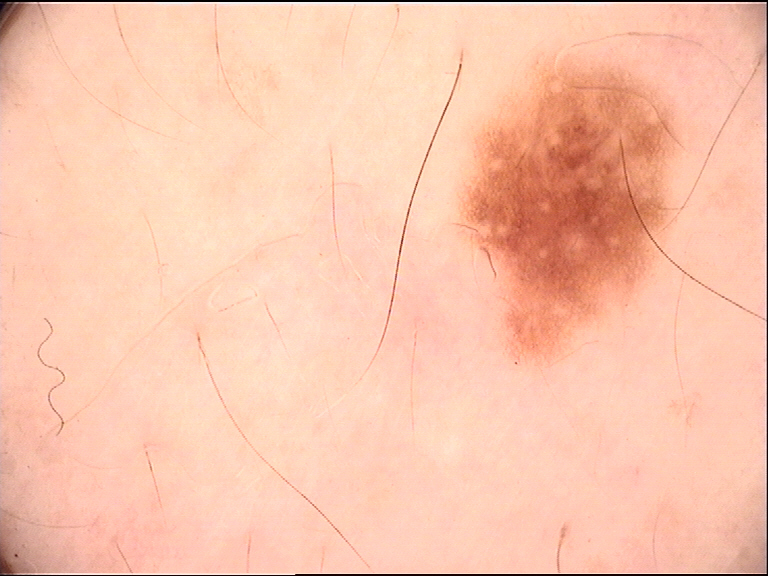modality = dermoscopy, diagnosis = dysplastic junctional nevus (expert consensus).